The patient is Fitzpatrick phototype IV; the chart notes no pesticide exposure; a clinical photograph of a skin lesion; a male patient in their early 80s — 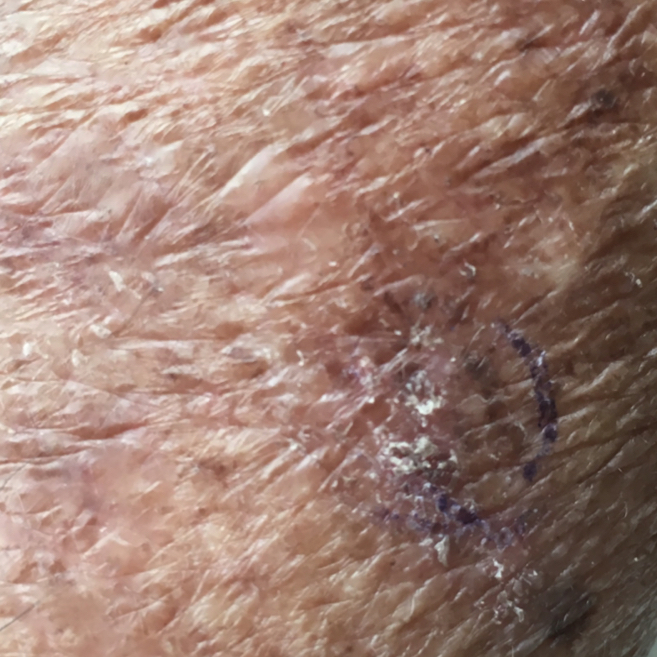The lesion is located on a forearm.
The lesion measures approximately 10 × 7 mm.
The patient describes that the lesion itches, but has not bled.
The clinical impression was an actinic keratosis.